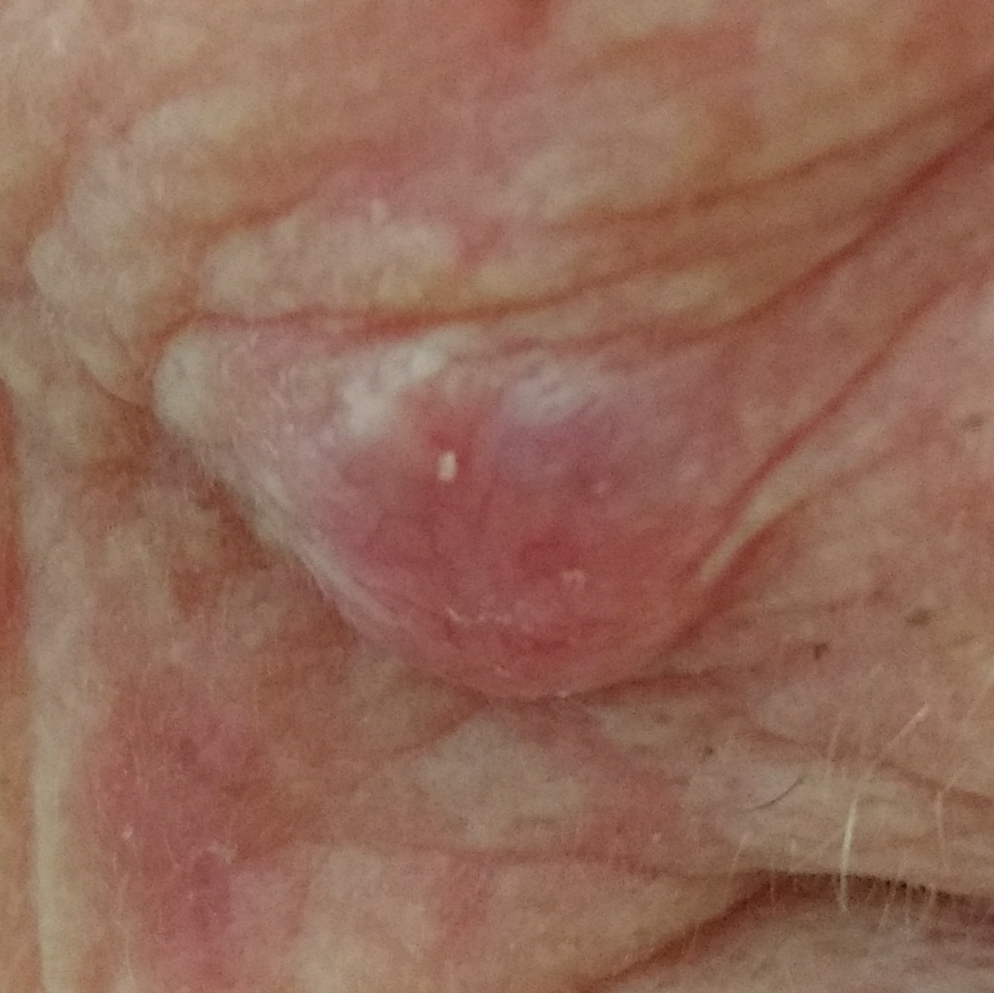A female subject in their late 80s. A smartphone photograph of a skin lesion. Located on the face. Per patient report, the lesion has changed, is elevated, itches, and has grown. Histopathology confirmed a basal cell carcinoma.